A skin lesion imaged with a dermatoscope:
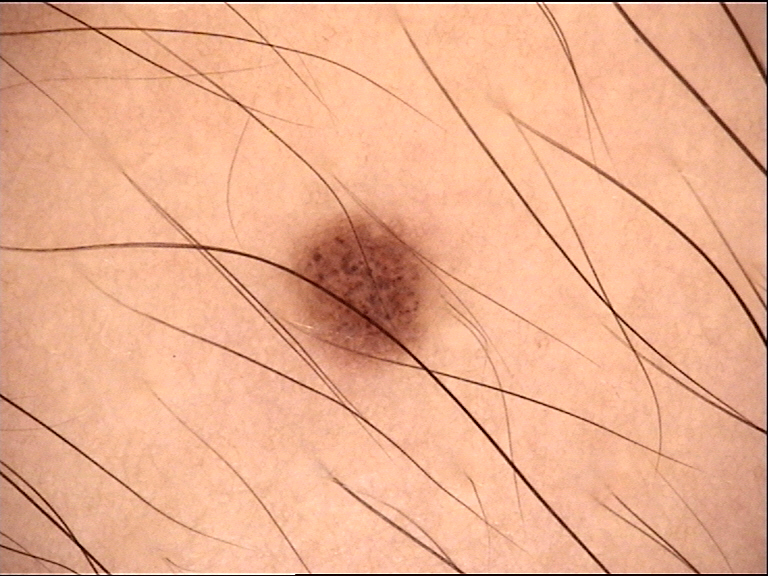The architecture is that of a banal lesion.
Labeled as a junctional nevus.